The patient is a female aged 40–49; this is a close-up image; located on the leg, top or side of the foot, sole of the foot and arm: 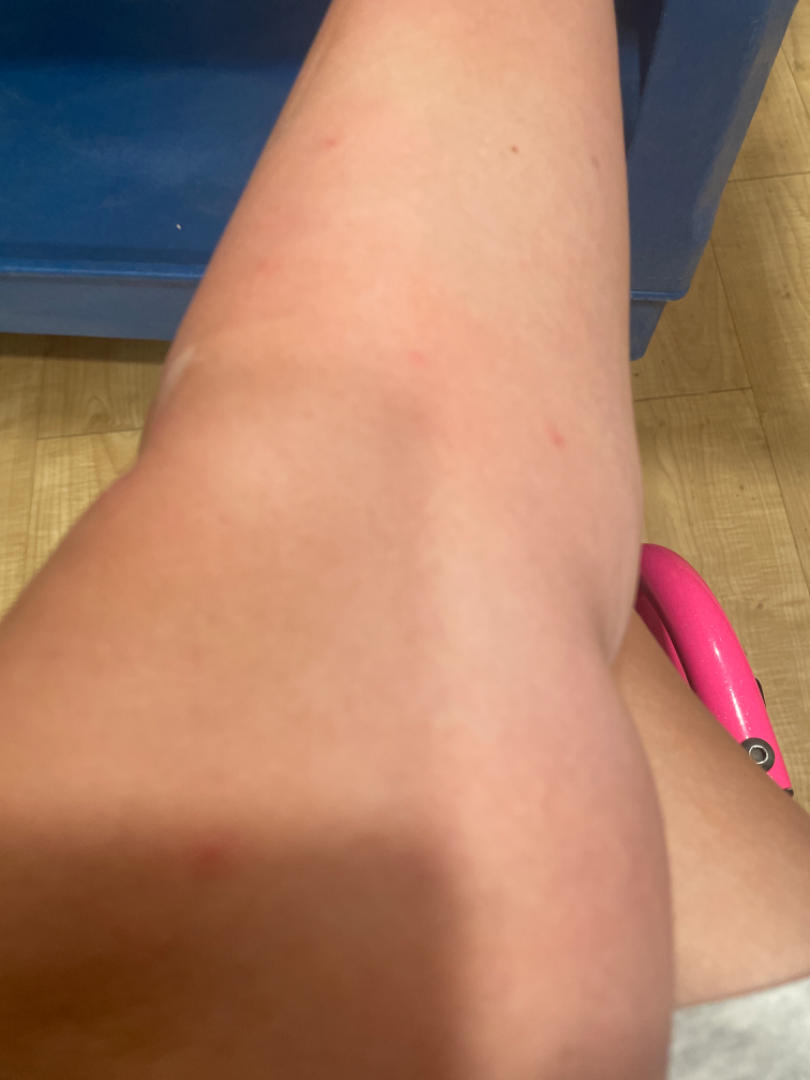The reviewing dermatologist was unable to assign a differential diagnosis from the image.